Located on the leg; an image taken at a distance; female contributor, age 18–29.
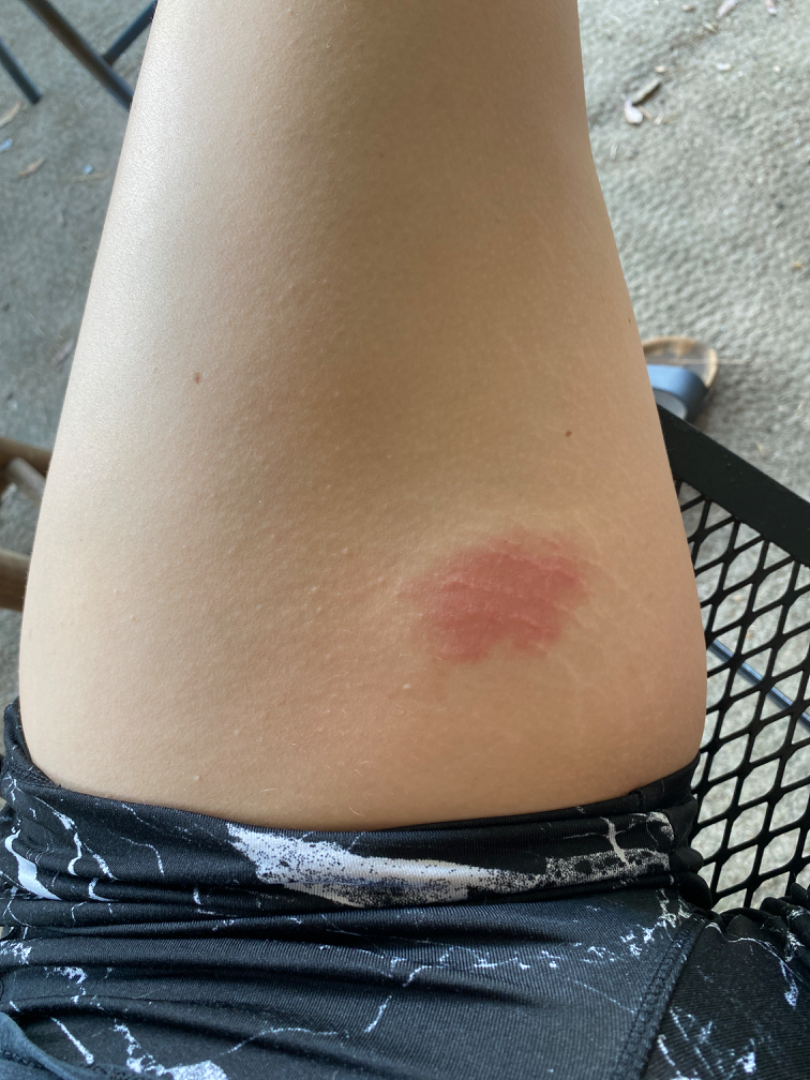In keeping with Acute dermatitis, NOS.